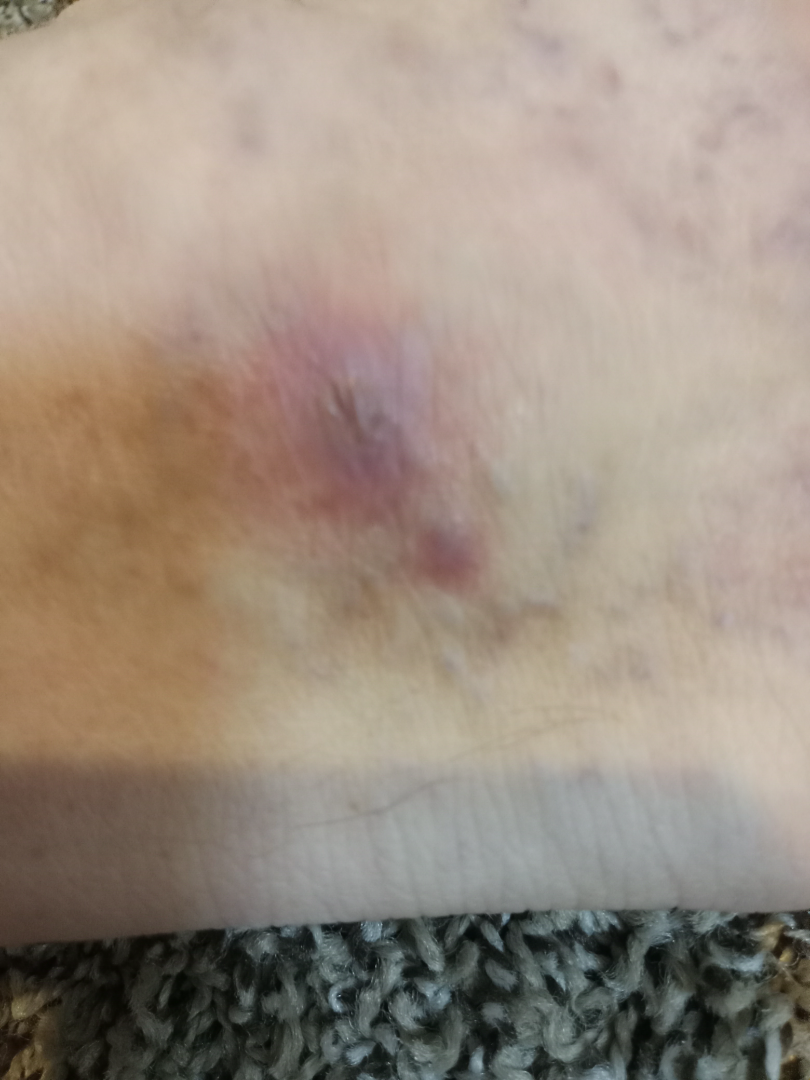duration: less than one week
texture:
  - flat
  - fluid-filled
body_site: top or side of the foot
systemic_symptoms: none reported
shot_type: at an angle
symptoms: bothersome appearance
differential:
  leading:
    - Venous Stasis Ulcer